Texture is reported as raised or bumpy and fluid-filled · a close-up photograph · the contributor is a male aged 18–29 · present for less than one week · symptoms reported: enlargement, itching, darkening and bothersome appearance:
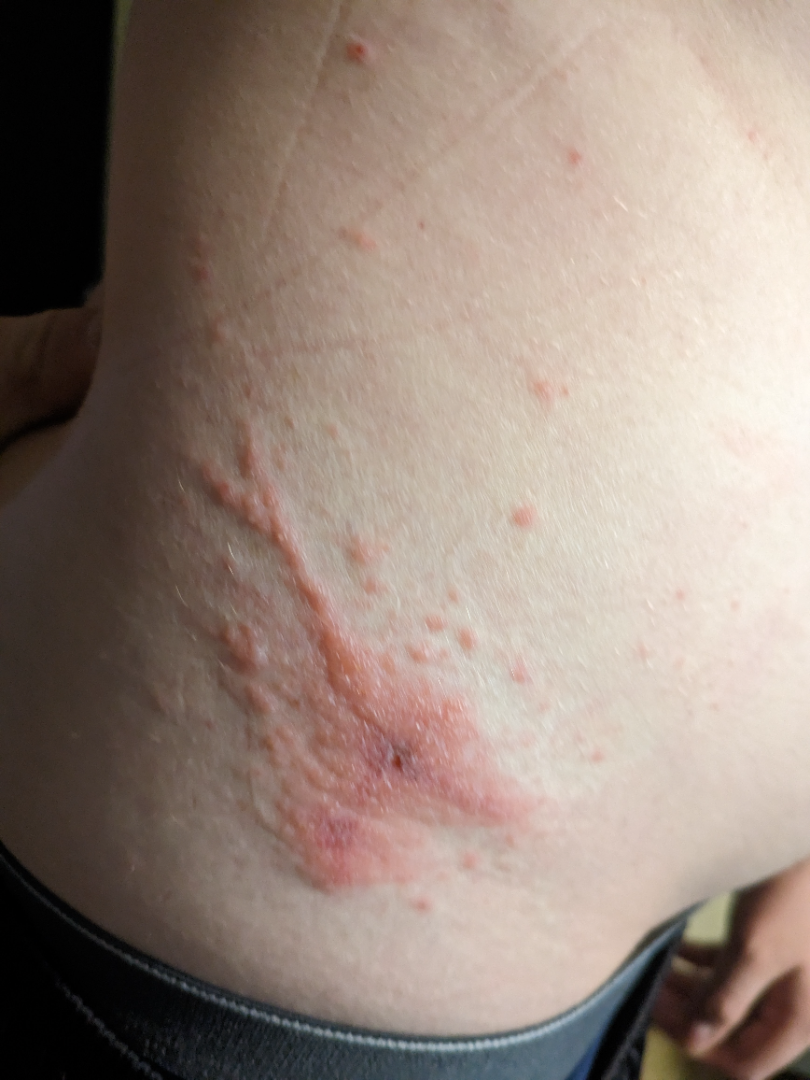Findings:
Consistent with Allergic Contact Dermatitis.